Texture is reported as raised or bumpy, a close-up photograph, reported duration is about one day, the patient reported no systemic symptoms, the front of the torso is involved: 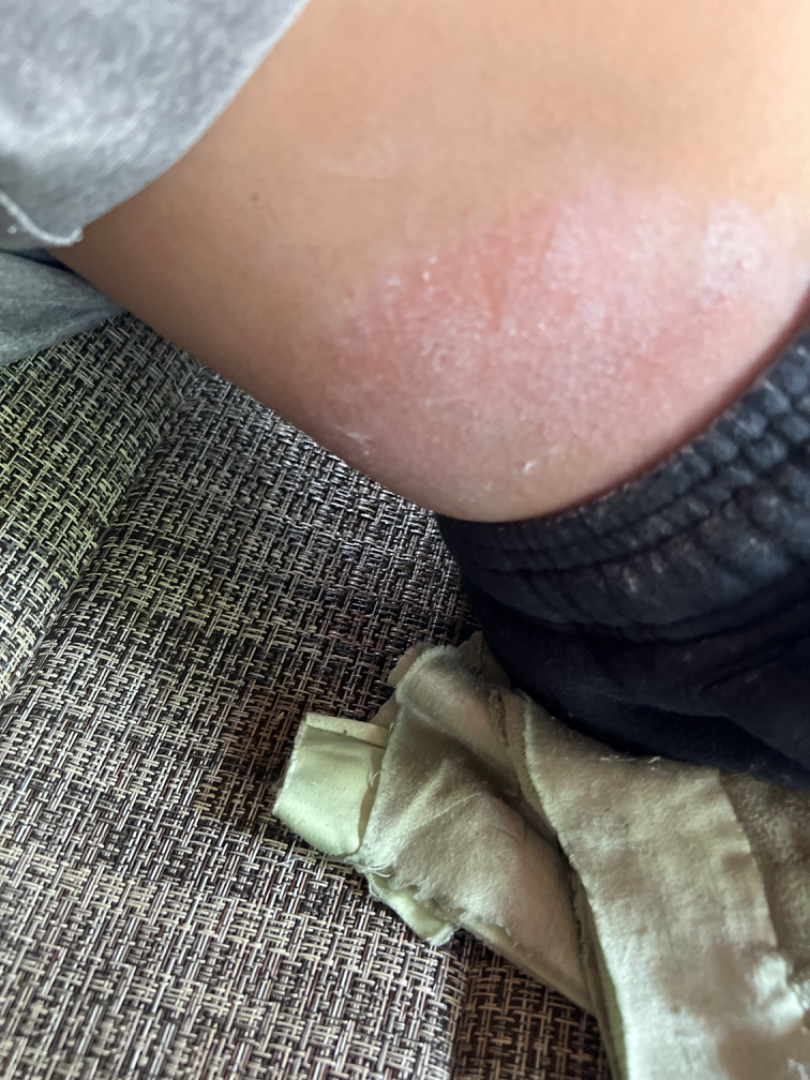  differential:
    Allergic Contact Dermatitis: 0.67
    Irritant Contact Dermatitis: 0.33